An image taken at a distance; the top or side of the foot is involved — 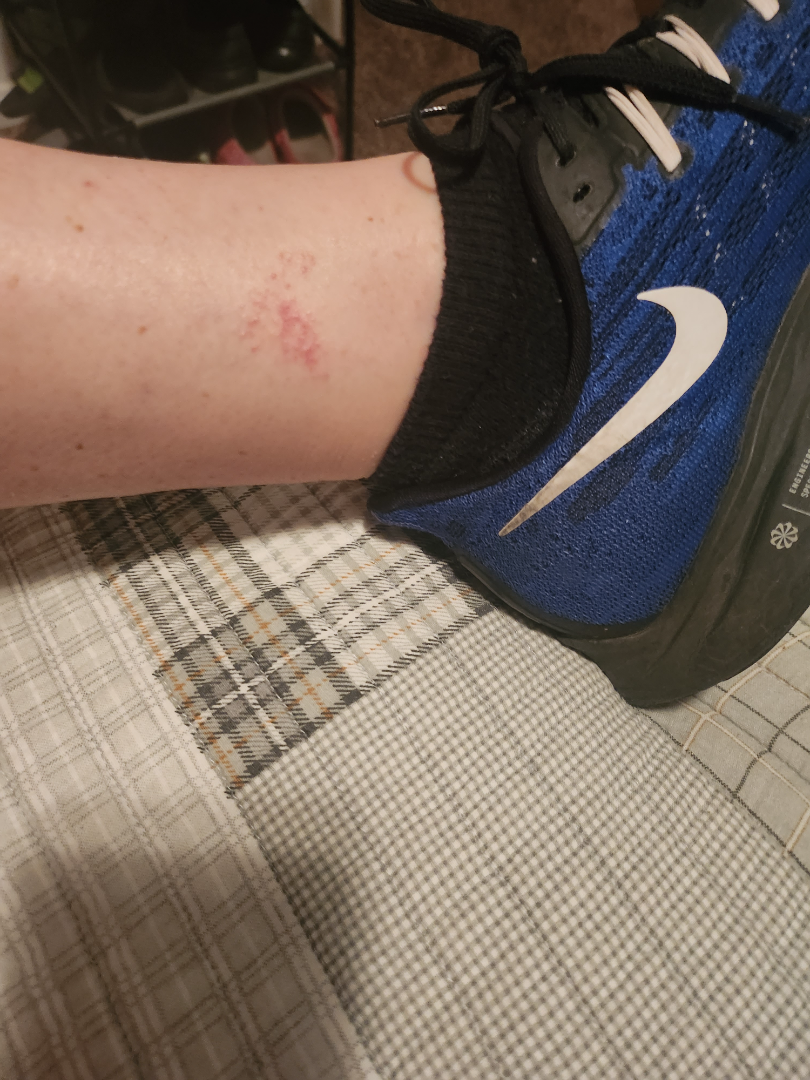Impression: The reviewer was unable to grade this case for skin condition.